This image was taken at an angle:
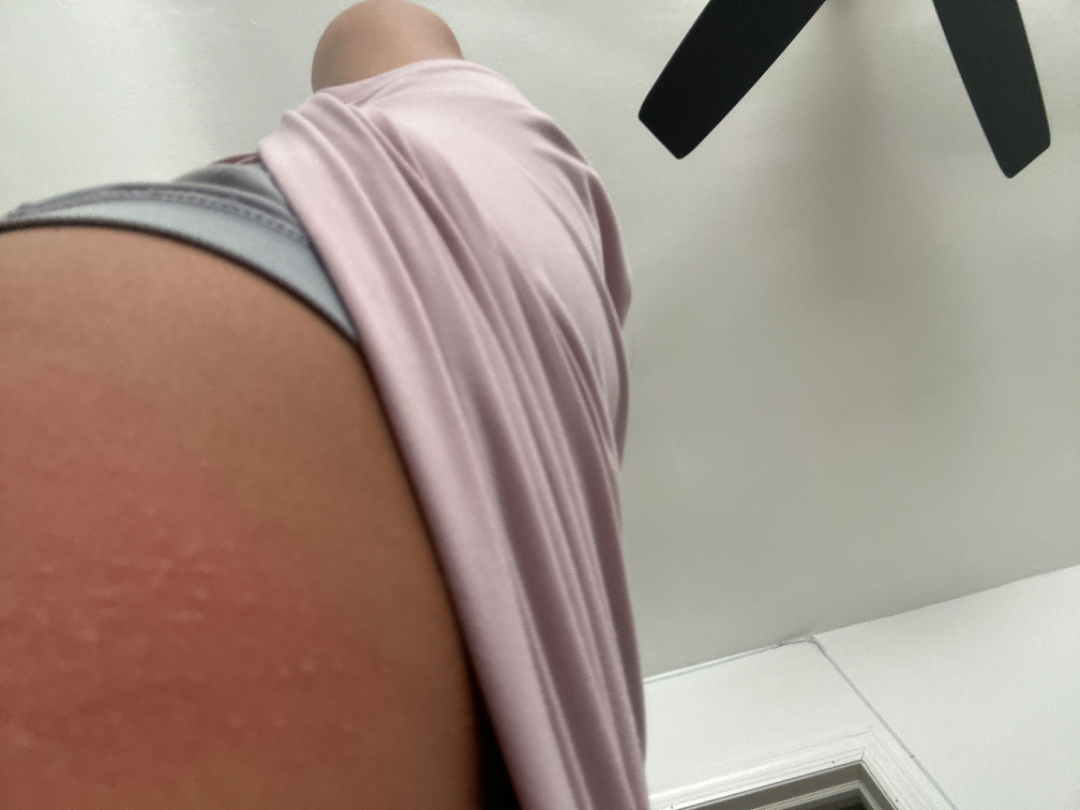assessment = could not be assessed
reported symptoms = itching
patient's own categorization = skin that appeared healthy to them
lesion texture = raised or bumpy
present for = about one day